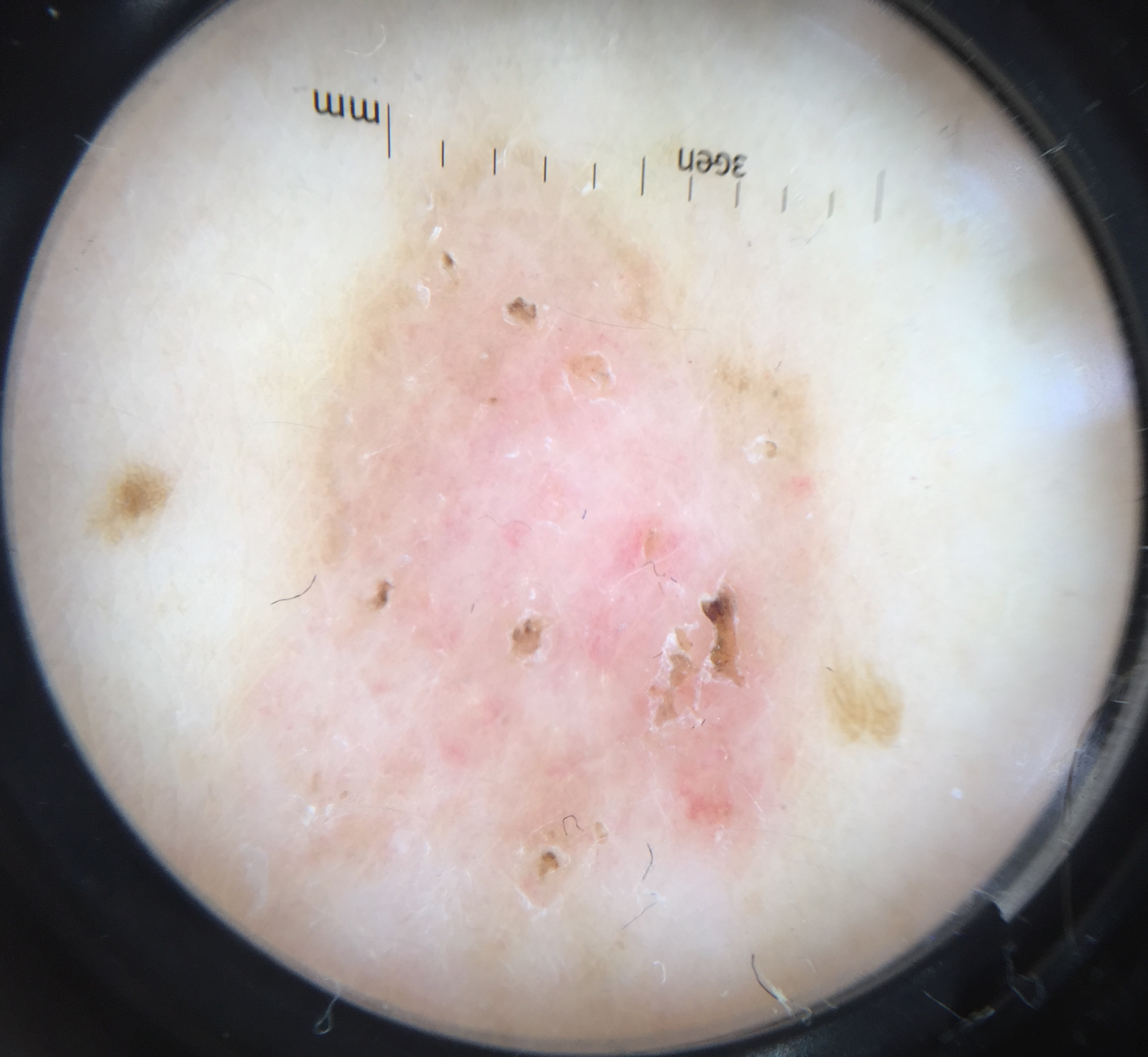Findings:
A dermoscopic image of a skin lesion.
Pathology:
Biopsy-confirmed as a keratinocytic, malignant lesion — a basal cell carcinoma.